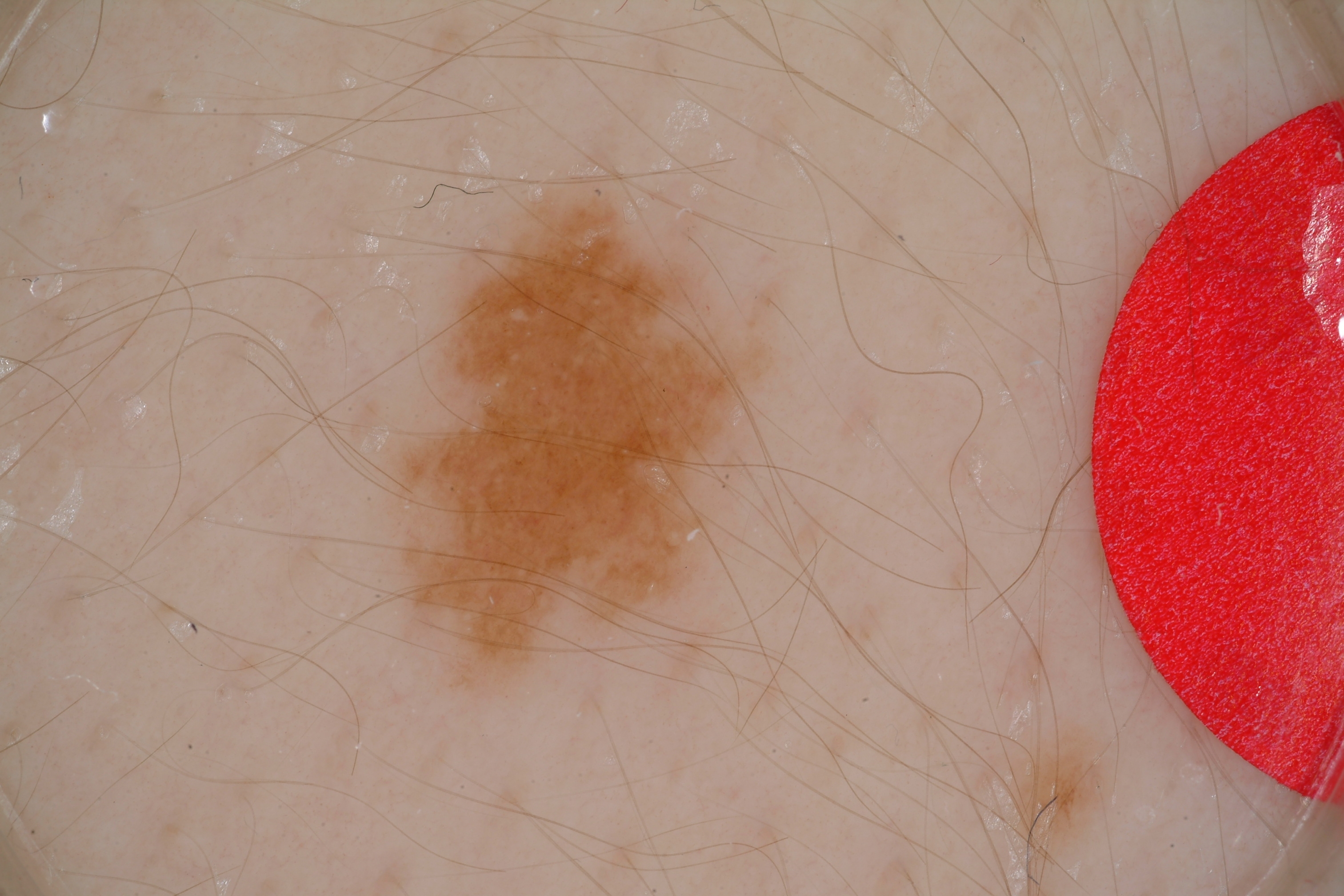Case summary:
The patient is a male approximately 15 years of age. A dermoscopic close-up of a skin lesion. The lesion is bounded by left=381, top=171, right=784, bottom=699. Dermoscopic review identifies milia-like cysts; no streaks, pigment network, negative network, or globules.
Assessment:
Expert review diagnosed this as a melanocytic nevus.